Close-up view. The lesion involves the arm.
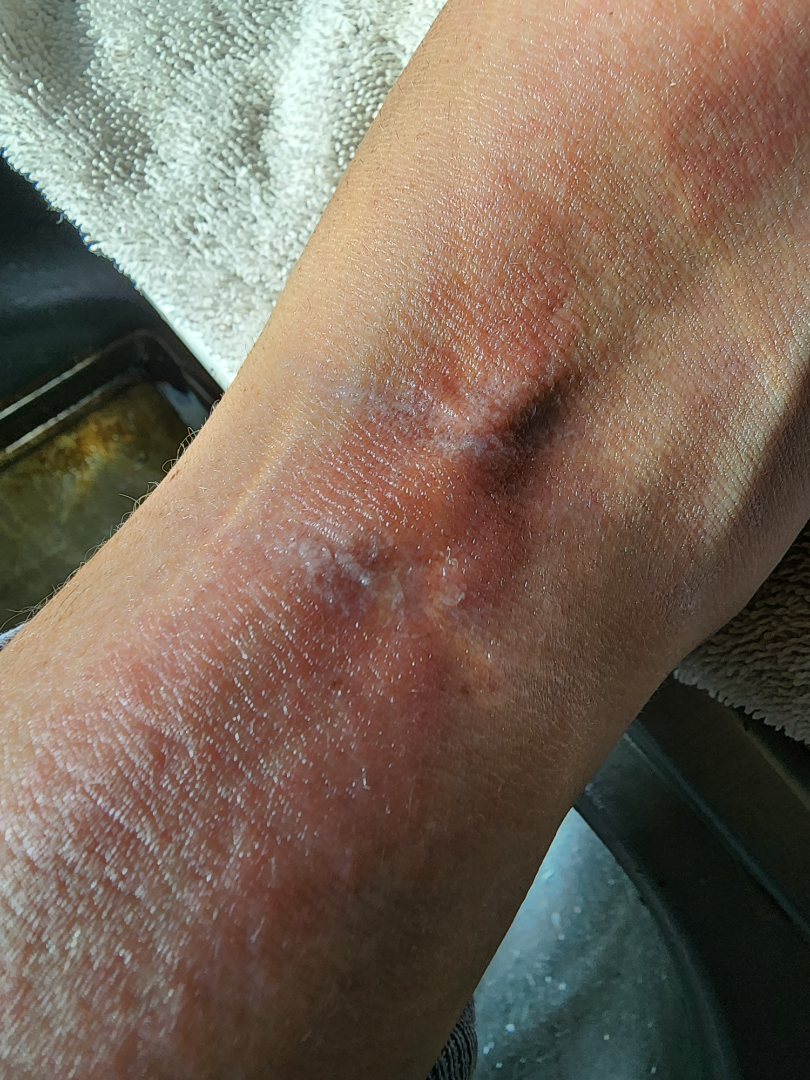Case summary:
- assessment — not assessable